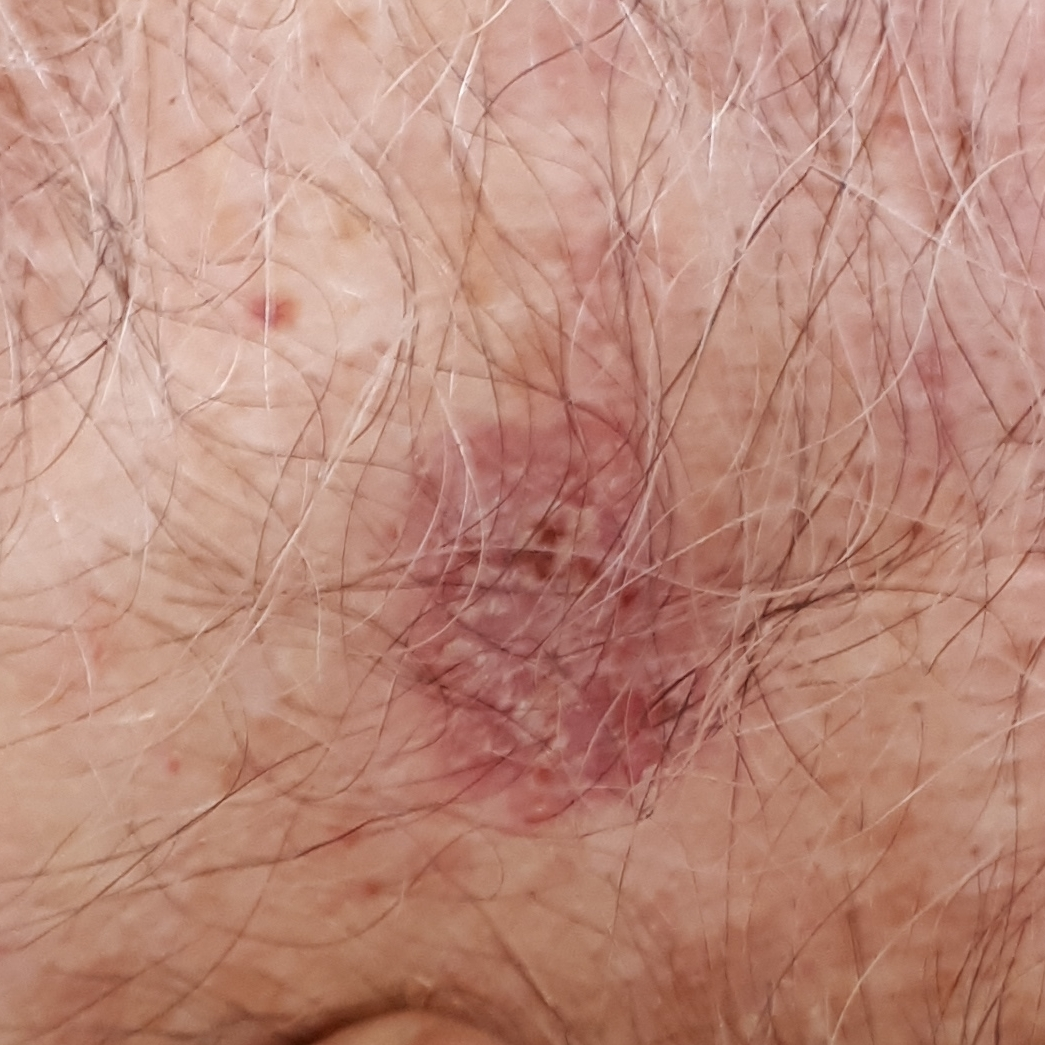A patient in their mid-70s. A smartphone photograph of a skin lesion. The lesion is located on the chest. By the patient's account, the lesion itches. The consensus clinical diagnosis was an actinic keratosis.